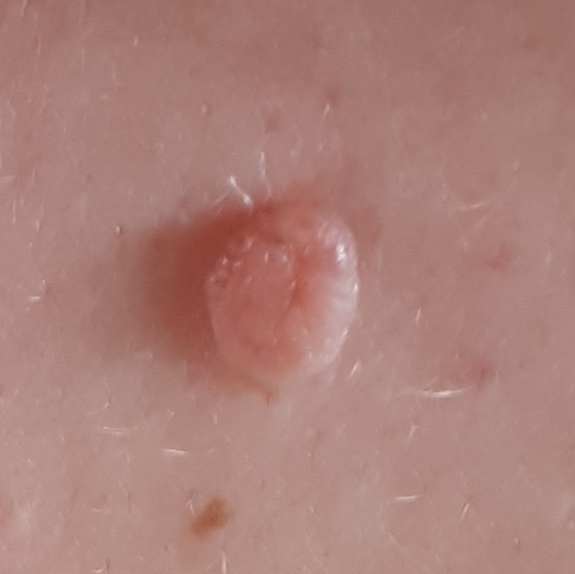Findings: A patient 32 years of age. A clinical photo of a skin lesion taken with a smartphone. Located on the back. Per patient report, the lesion is elevated, but does not hurt and has not grown. Impression: Consistent with a nevus.